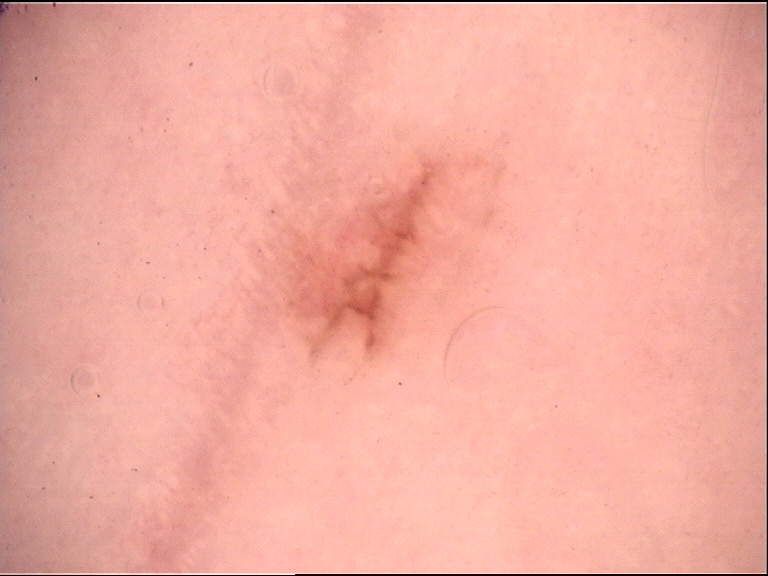Q: What is the diagnosis?
A: acral junctional nevus (expert consensus)